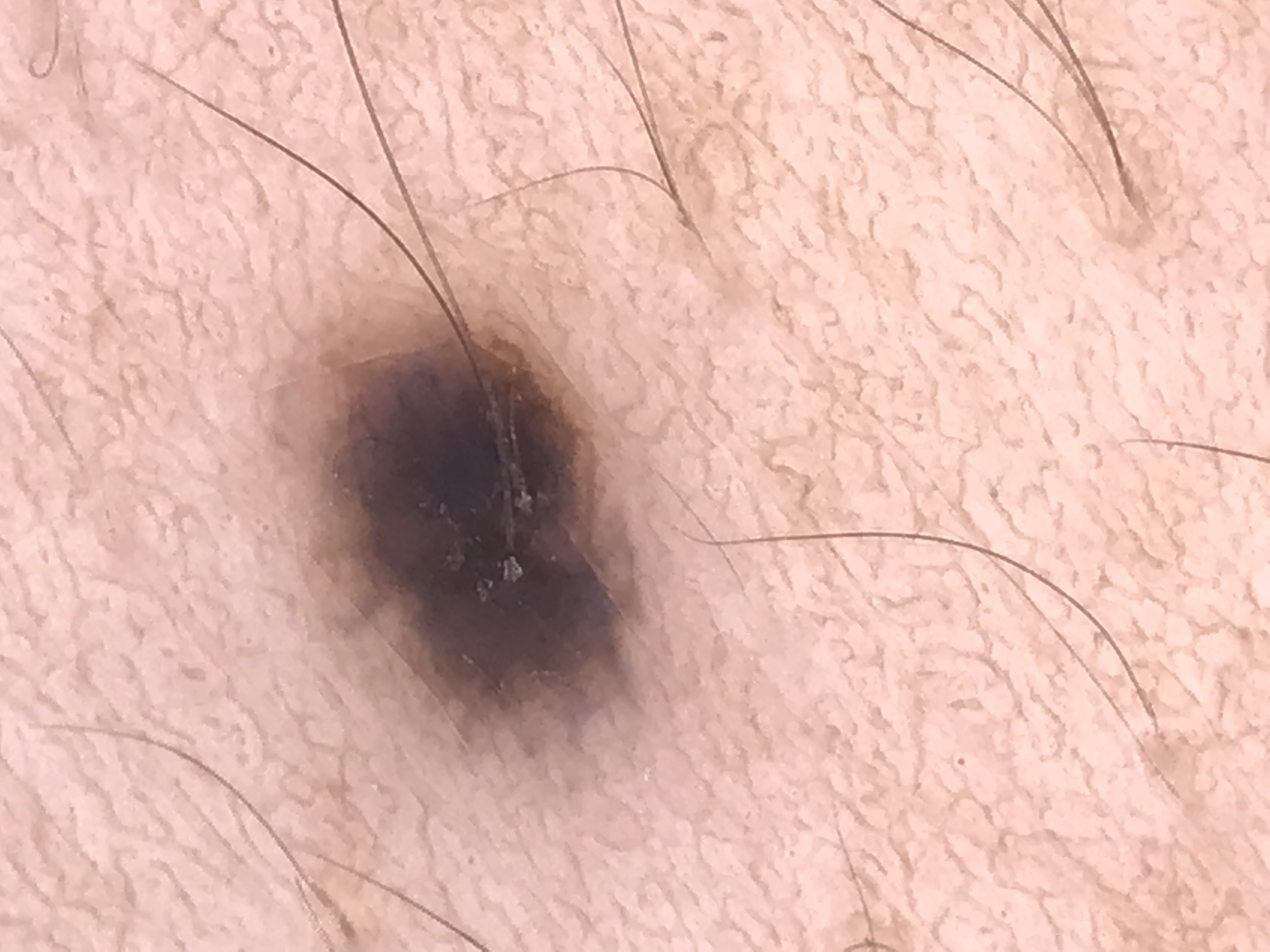Q: What is this lesion?
A: blue nevus (expert consensus)